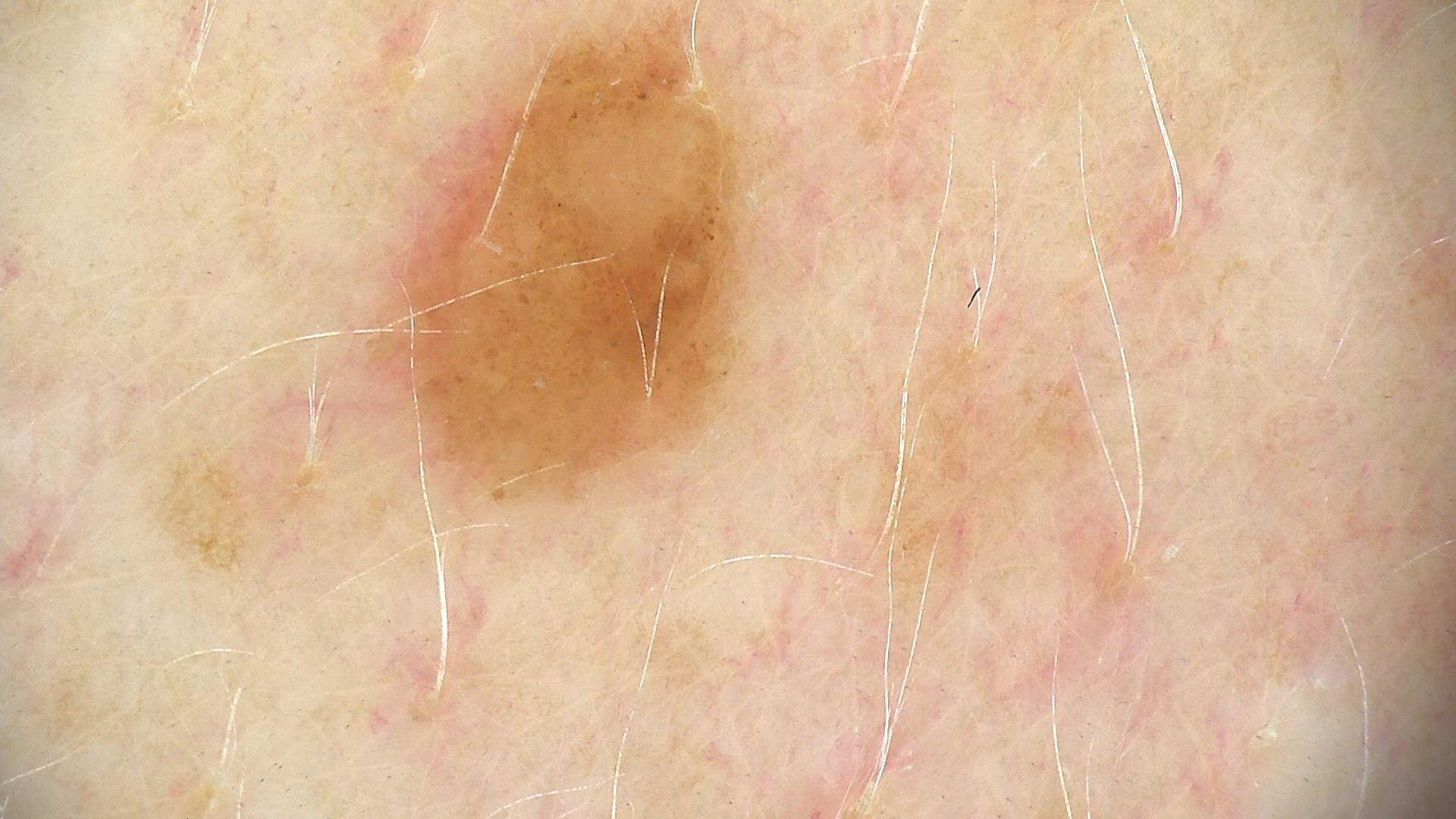imaging: dermatoscopy | assessment: dysplastic compound nevus (expert consensus).